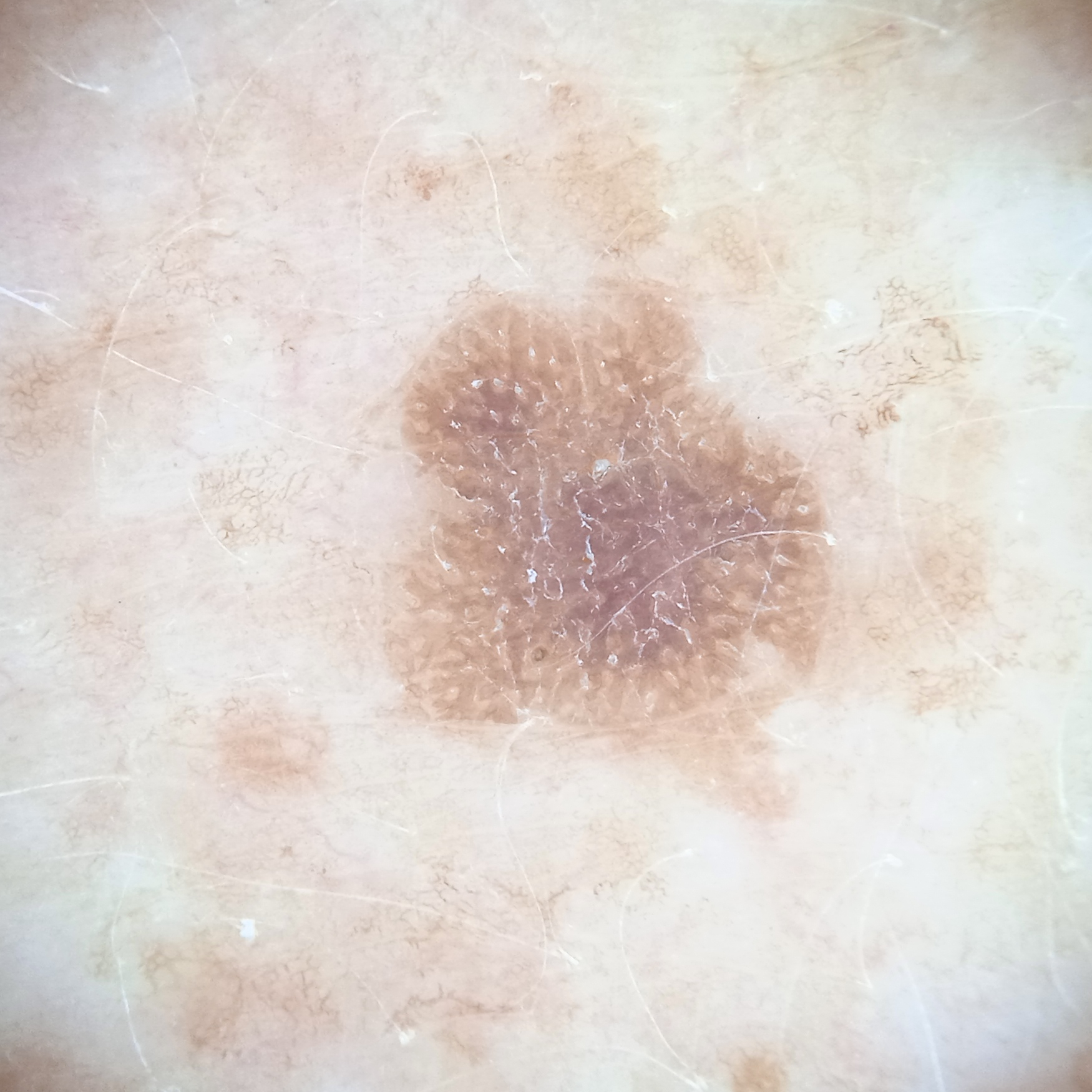sun reaction: skin tans without first burning
nevus count: numerous melanocytic nevi
subject: female, age 78
location: the back
diagnosis: seborrheic keratosis (dermatologist consensus)